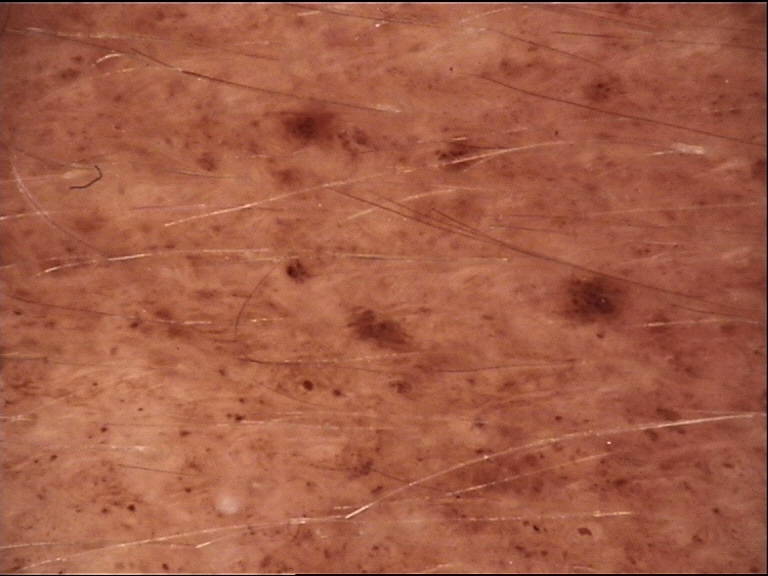<dermoscopy>
  <image>dermoscopy</image>
  <lesion_type>
    <main_class>banal</main_class>
    <pattern>compound</pattern>
  </lesion_type>
  <diagnosis>
    <name>congenital compound nevus</name>
    <code>ccb</code>
    <malignancy>benign</malignancy>
    <super_class>melanocytic</super_class>
    <confirmation>expert consensus</confirmation>
  </diagnosis>
</dermoscopy>